A wide-field clinical photograph of a skin lesion · a female patient aged 78 to 82 · skin type II: 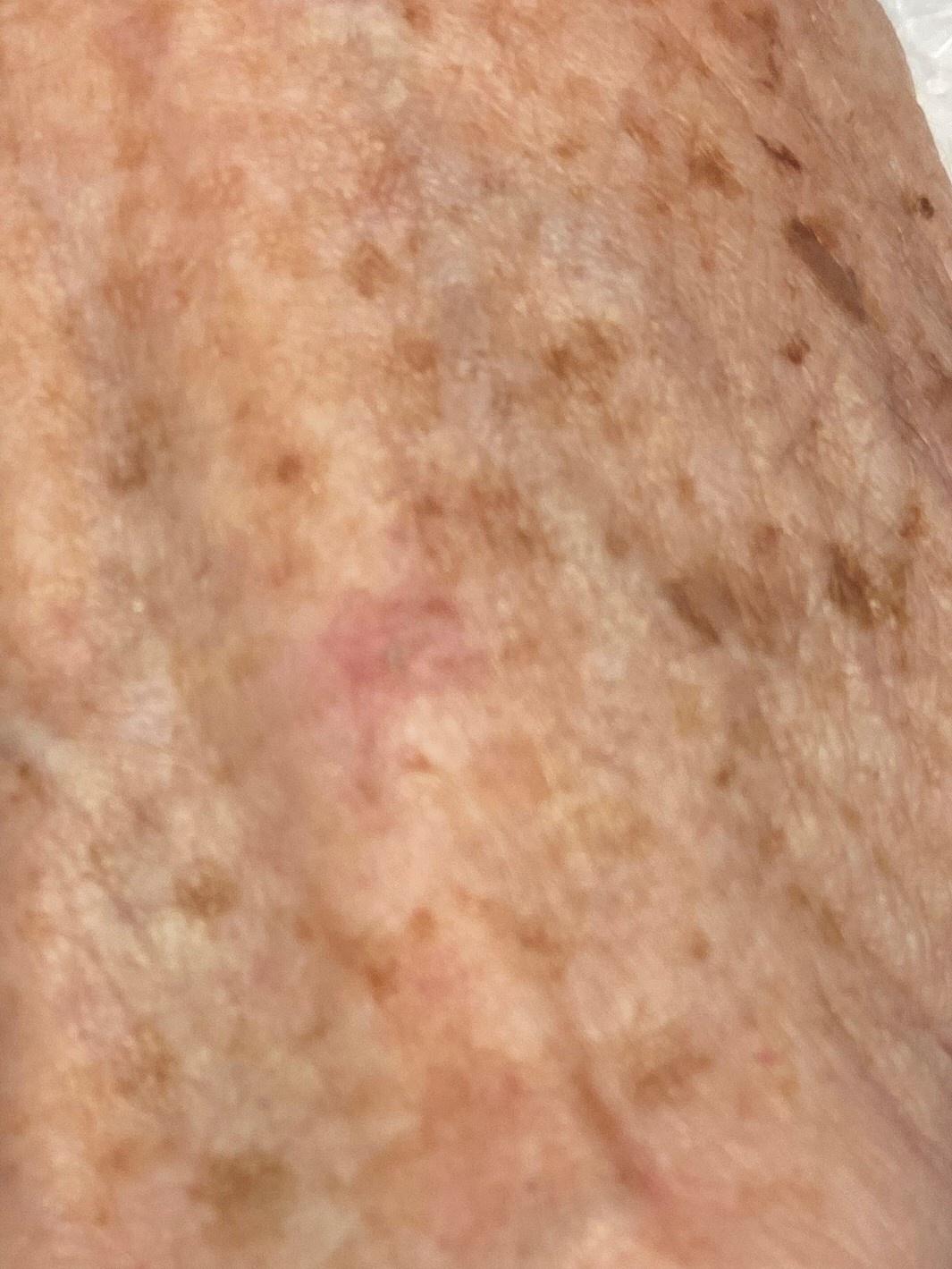Conclusion:
Histopathological examination showed an epidermal proliferation — a squamous cell carcinoma.